A dermoscopy image of a single skin lesion.
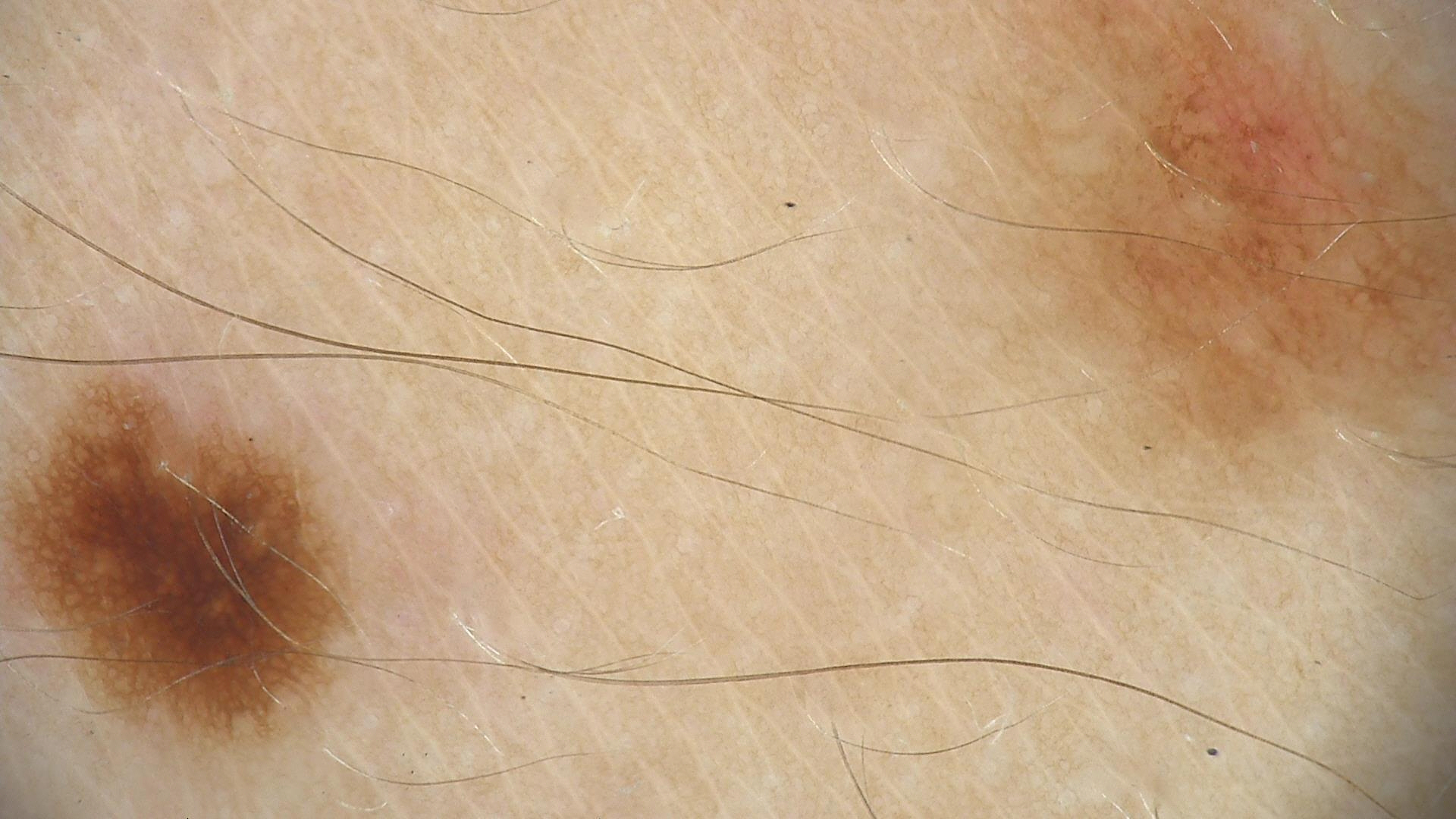class = dysplastic junctional nevus (expert consensus).